A male patient, this is a dermoscopic photograph of a skin lesion: 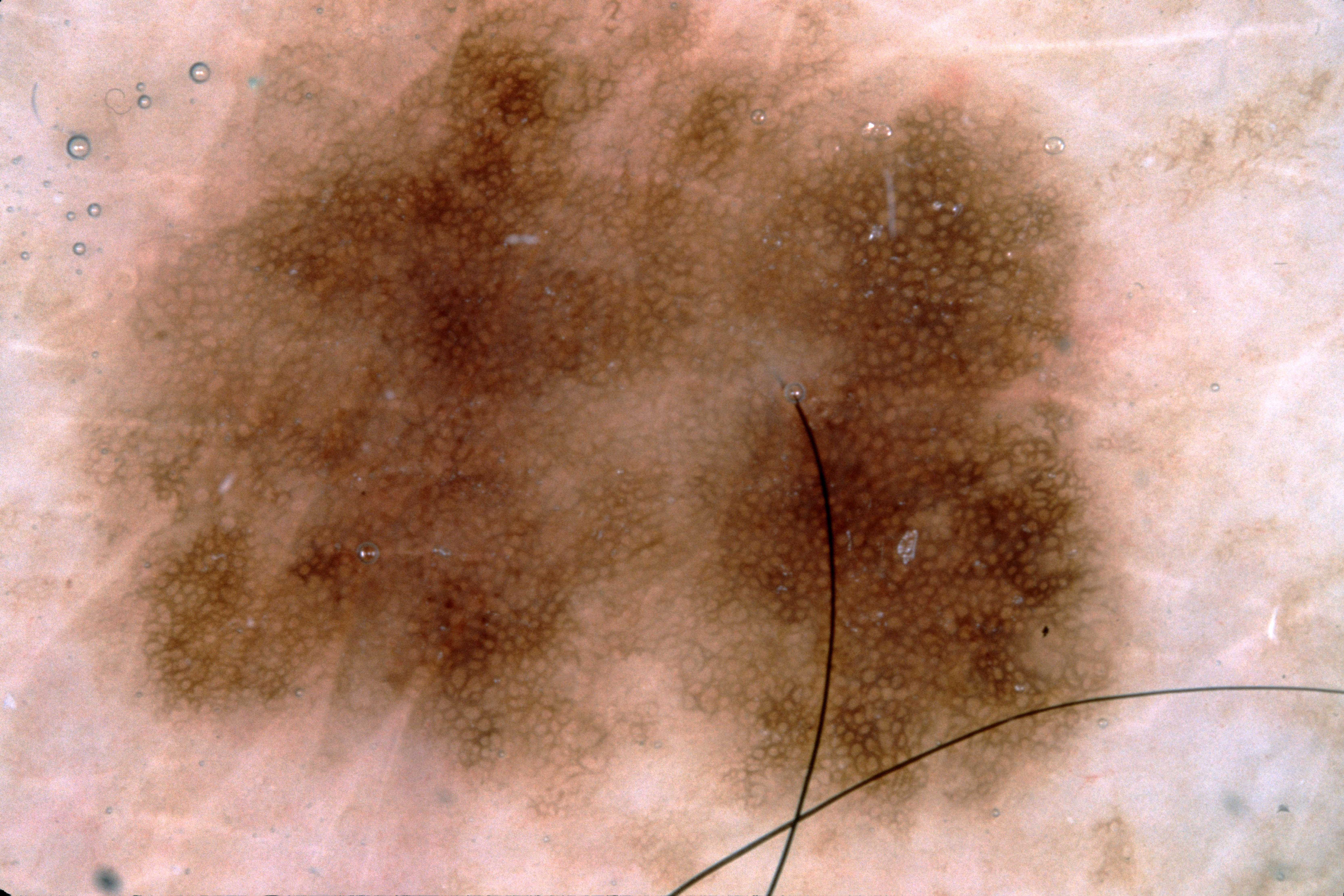The lesion is bounded by x1=55 y1=2 x2=1144 y2=895.
The lesion takes up about 68% of the image.
On dermoscopy, the lesion shows pigment network.
Clinically diagnosed as a melanocytic nevus.